The patient described the issue as a rash. No relevant lesion symptoms reported. No relevant systemic symptoms. The subject is a female aged 18–29. The photograph was taken at a distance. Located on the back of the hand. The patient indicates the lesion is raised or bumpy.
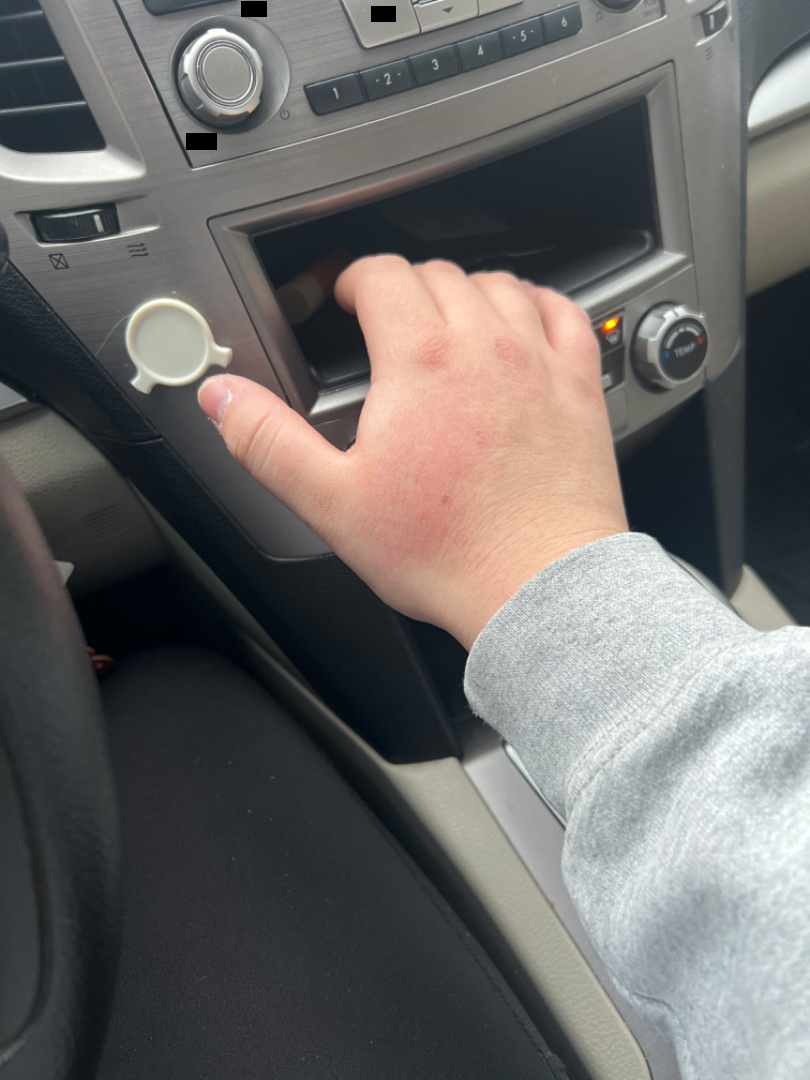Q: What conditions are considered?
A: the leading impression is Irritant Contact Dermatitis